A dermoscopic close-up of a skin lesion.
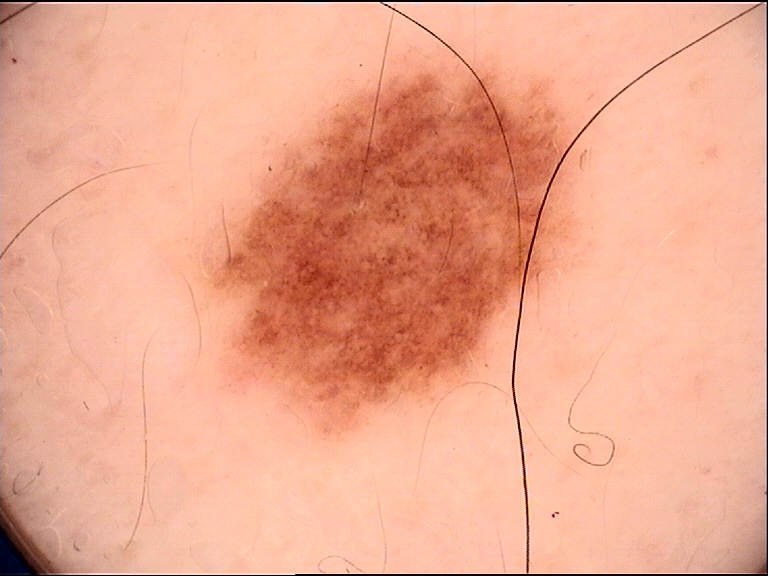<case>
<diagnosis>
<name>dysplastic junctional nevus</name>
<code>jd</code>
<malignancy>benign</malignancy>
<super_class>melanocytic</super_class>
<confirmation>expert consensus</confirmation>
</diagnosis>
</case>